Dermoscopy of a skin lesion: 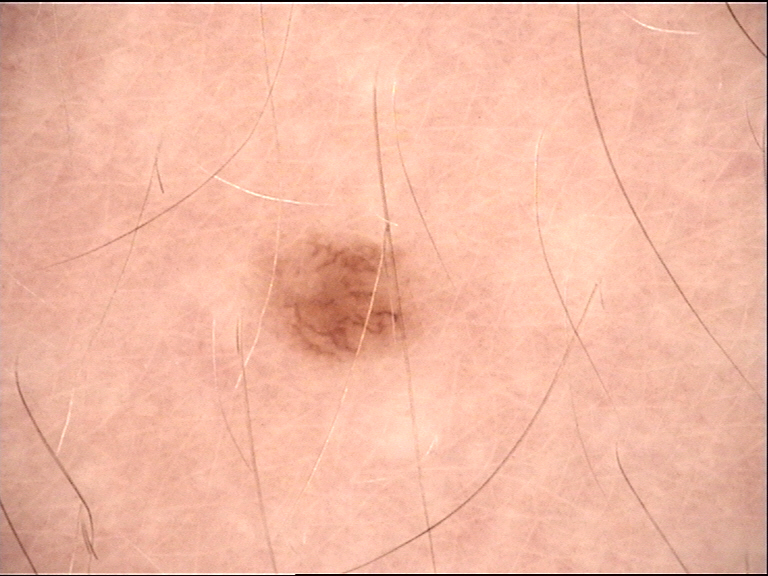diagnosis: dermal nevus (expert consensus).